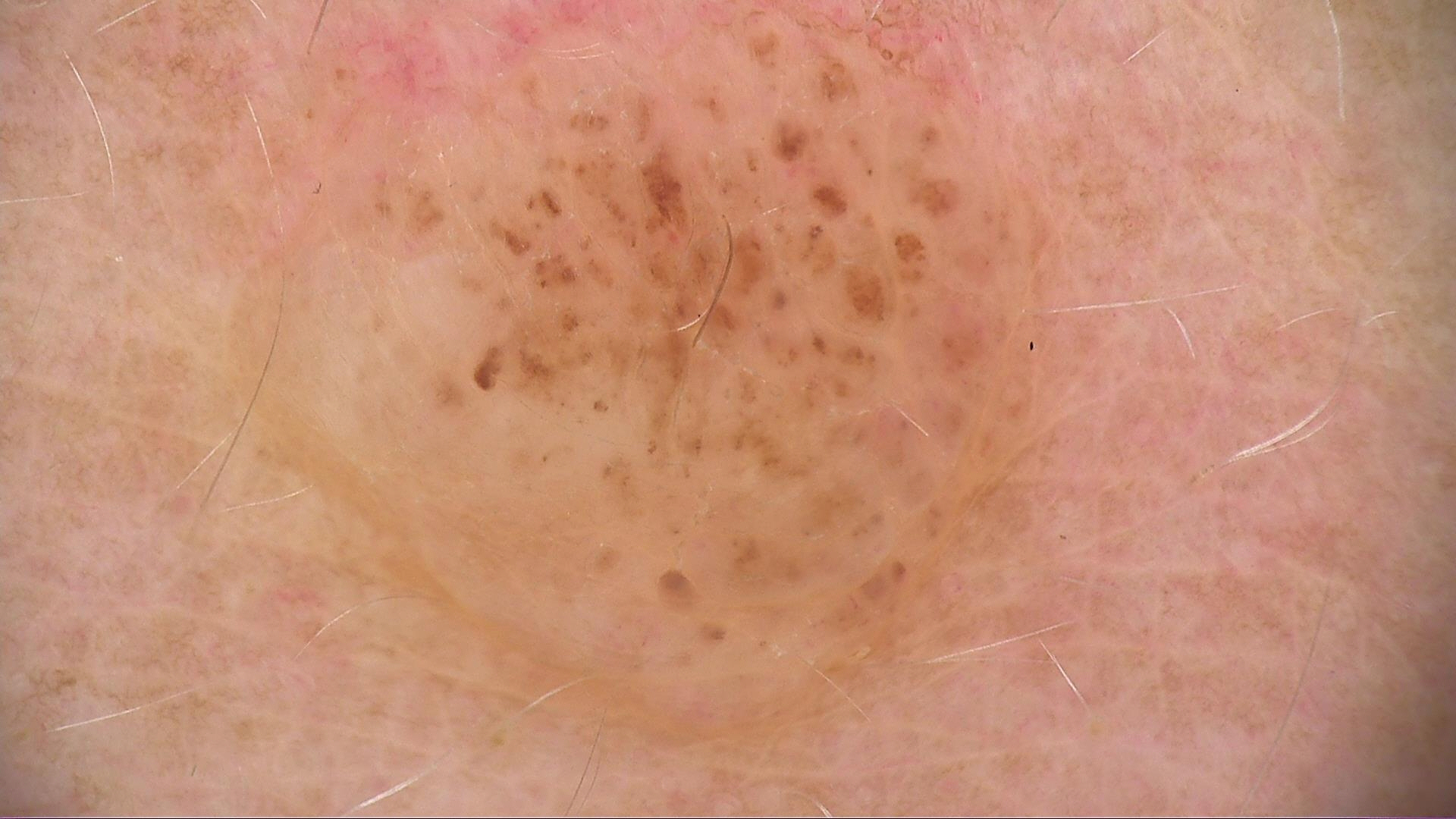image type = dermoscopy, subtype = banal, assessment = dermal nevus (expert consensus).